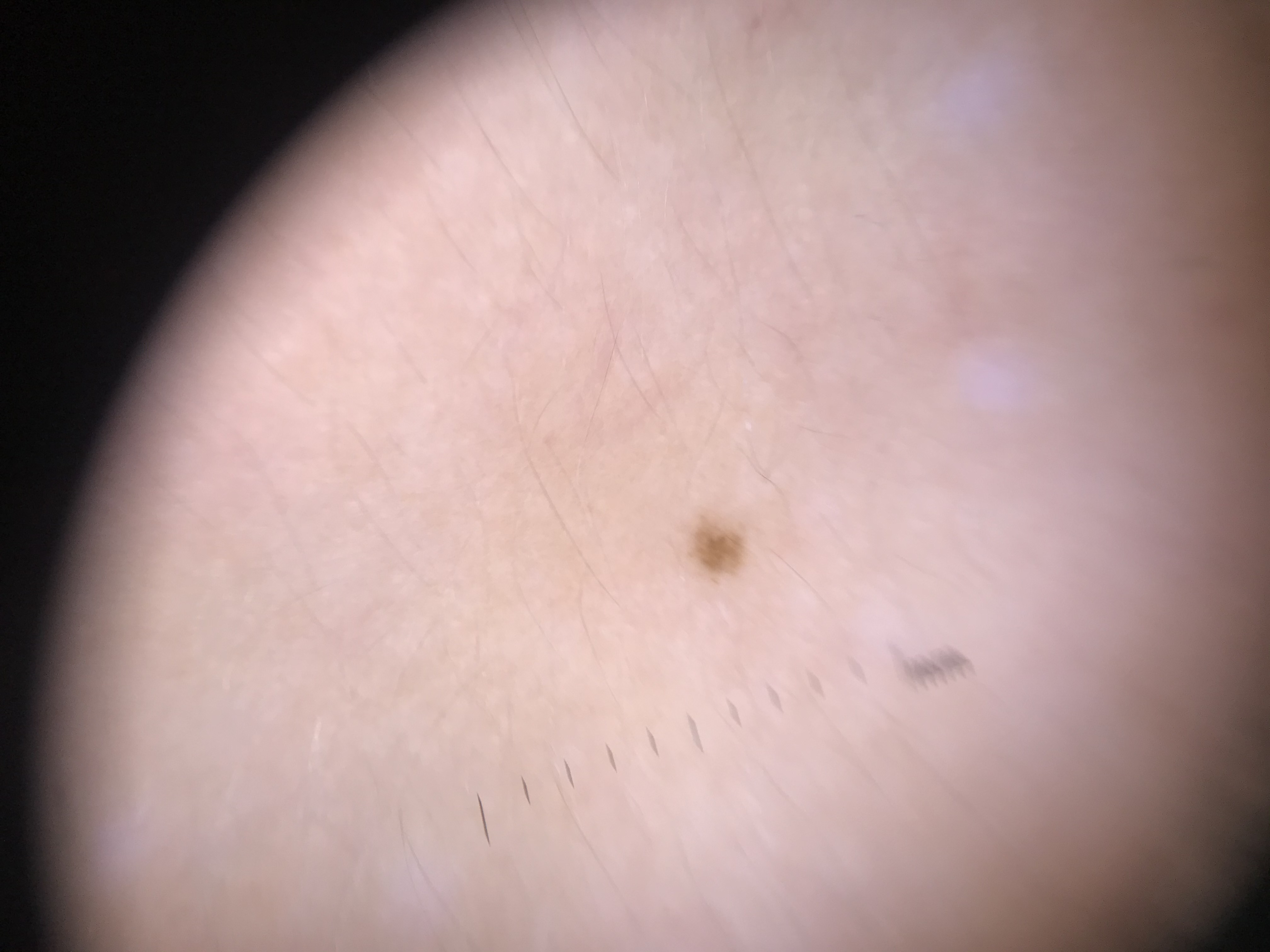Consistent with a junctional nevus.